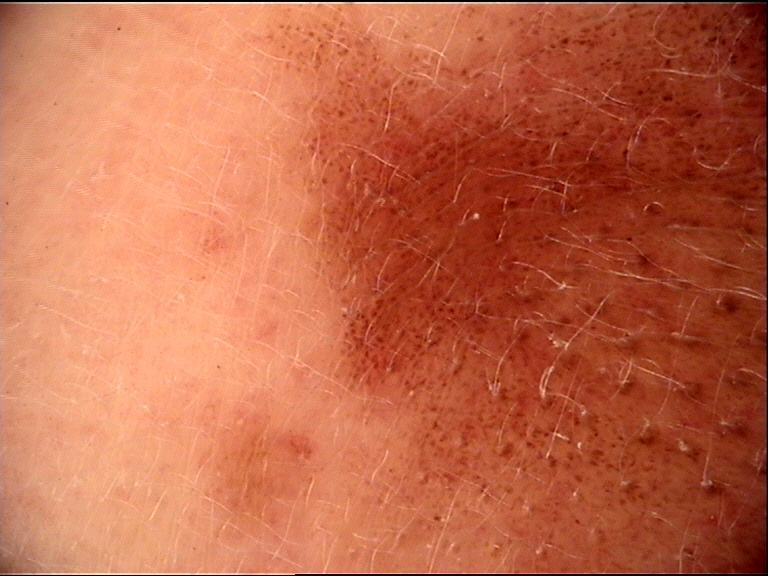Consistent with a congenital junctional nevus.